Dermoscopy of a skin lesion:
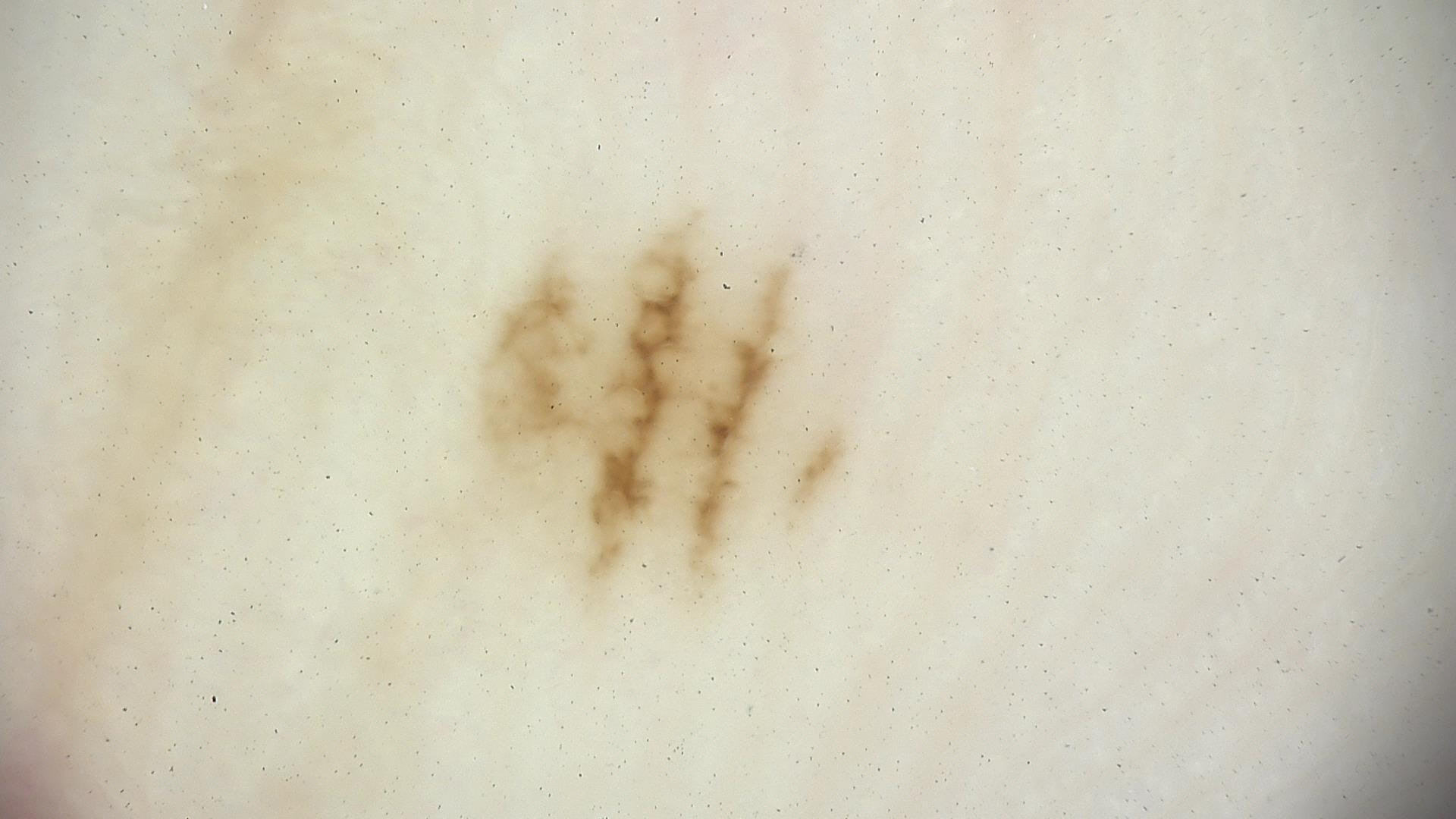| field | value |
|---|---|
| label | acral dysplastic junctional nevus (expert consensus) |